A male subject roughly 75 years of age · dermoscopy of a skin lesion · Fitzpatrick II:
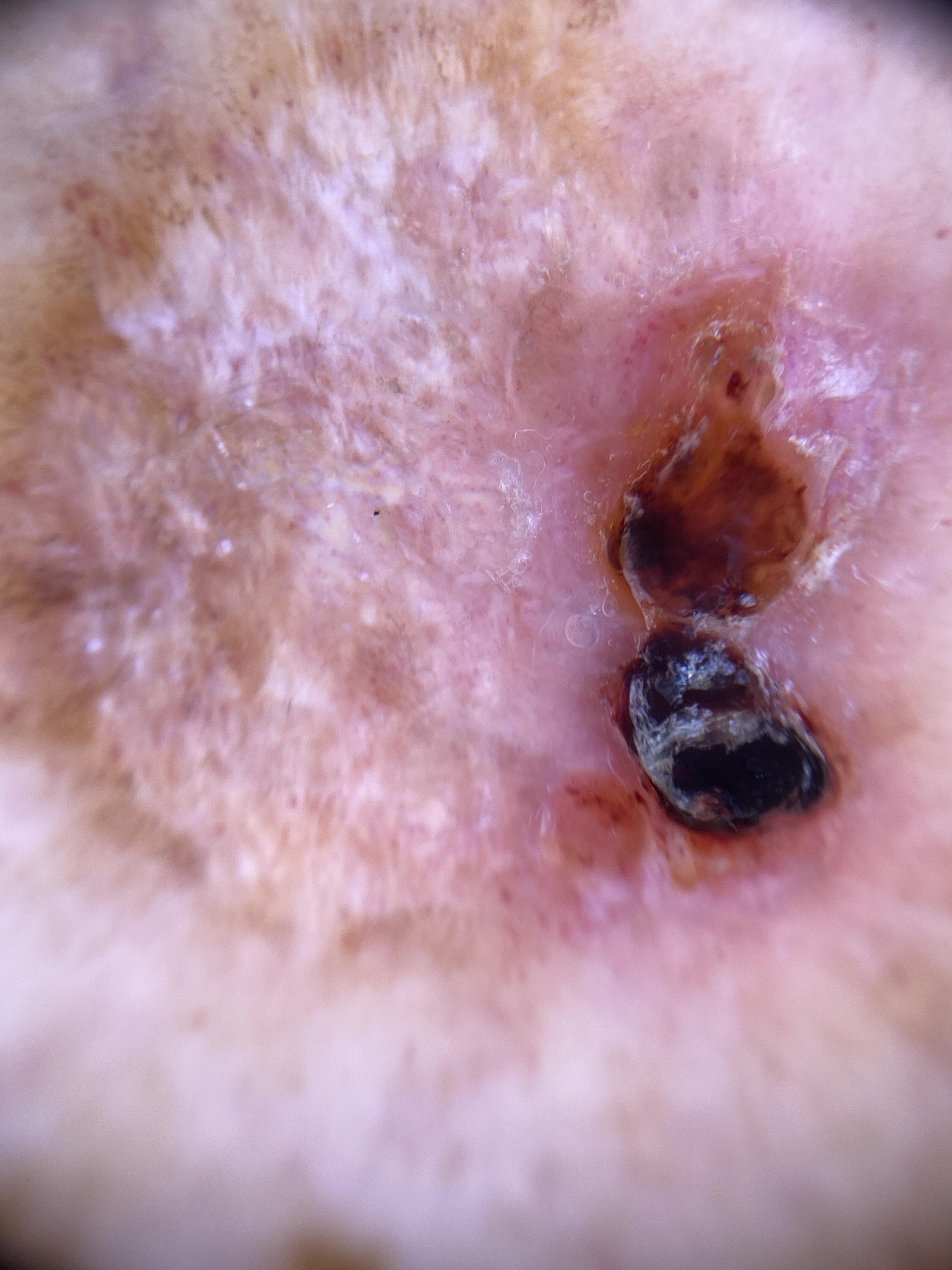Located on a lower extremity. Biopsy-confirmed as a malignant, adnexal lesion — a basal cell carcinoma.